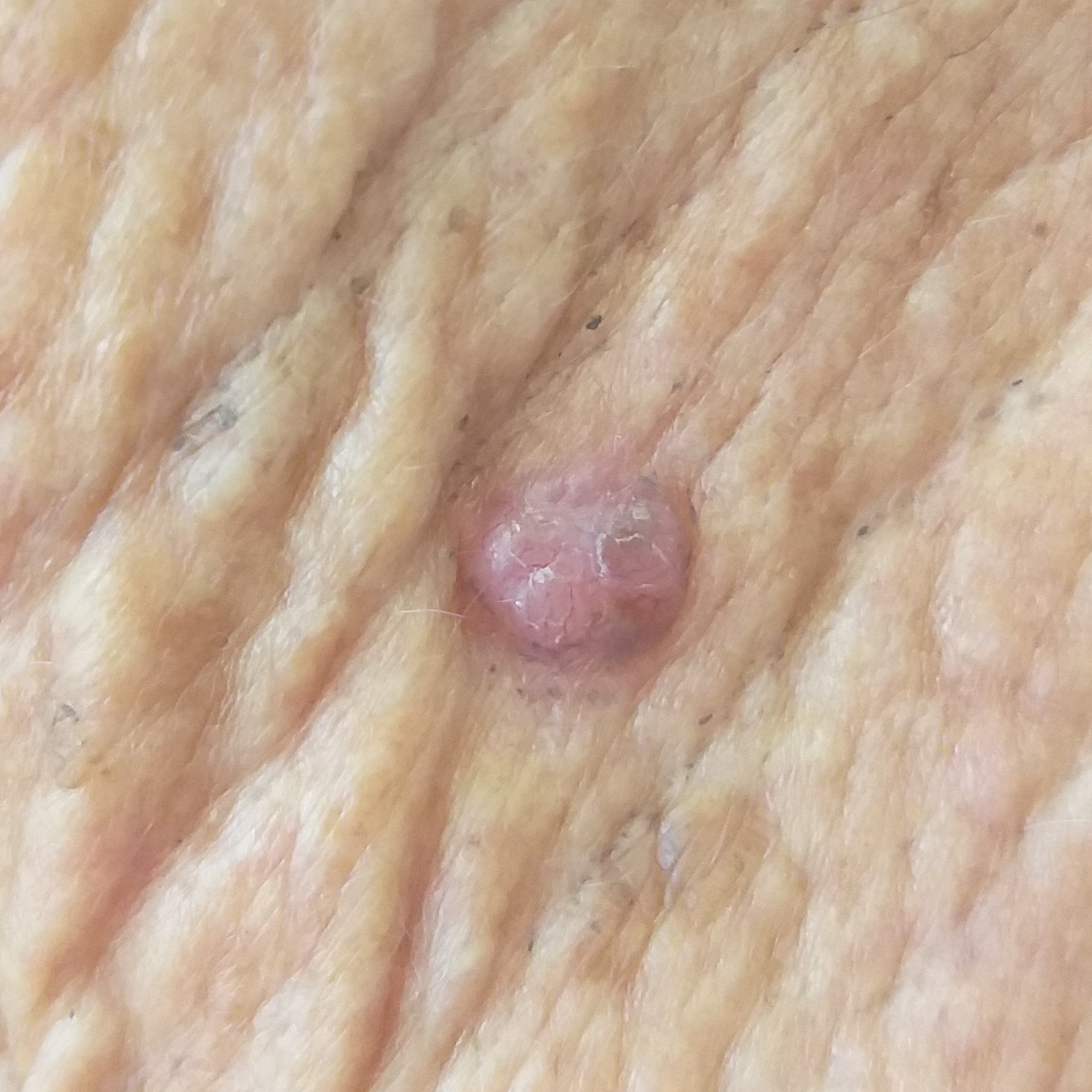Biopsy-confirmed as a basal cell carcinoma.